A dermoscopy image of a single skin lesion.
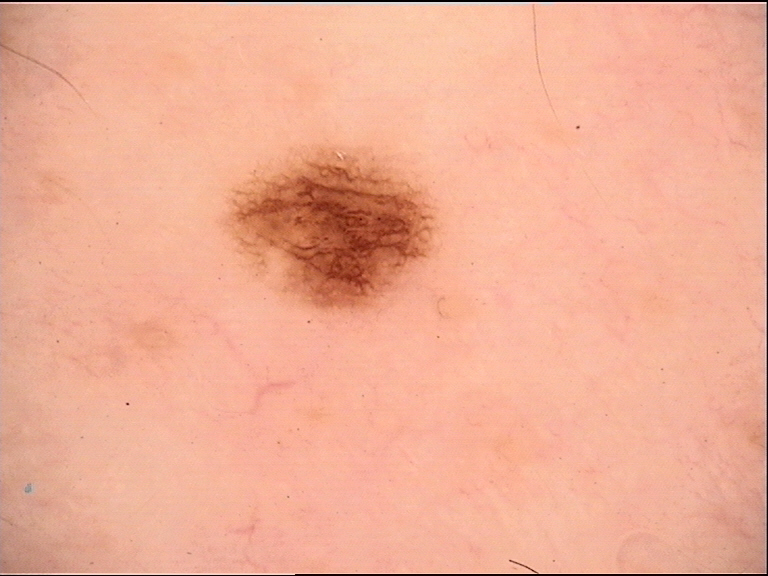<dermoscopy>
<diagnosis>
<name>dysplastic junctional nevus</name>
<code>jd</code>
<malignancy>benign</malignancy>
<super_class>melanocytic</super_class>
<confirmation>expert consensus</confirmation>
</diagnosis>
</dermoscopy>